Close-up view — 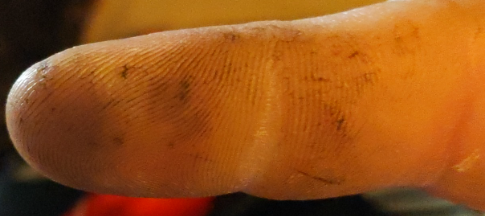– assessment: ungradable on photographic review
– described texture: raised or bumpy
– onset: less than one week
– associated systemic symptoms: joint pain